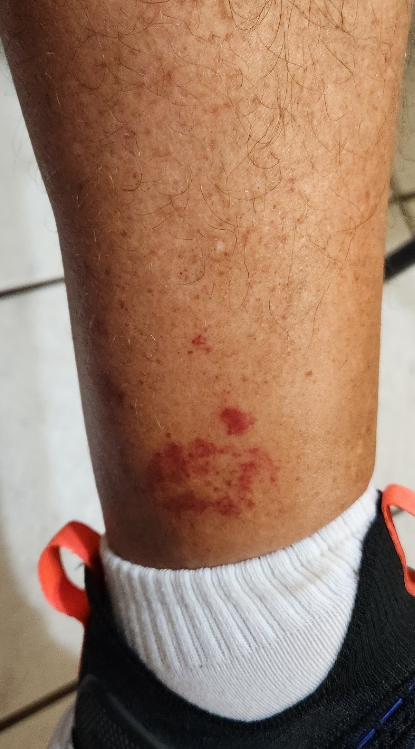Male patient, age 40–49. A close-up photograph. The lesion involves the leg. Reviewed remotely by one dermatologist: favoring Pigmented purpuric eruption; possibly ecchymoses; also raised was Leukocytoclastic Vasculitis.